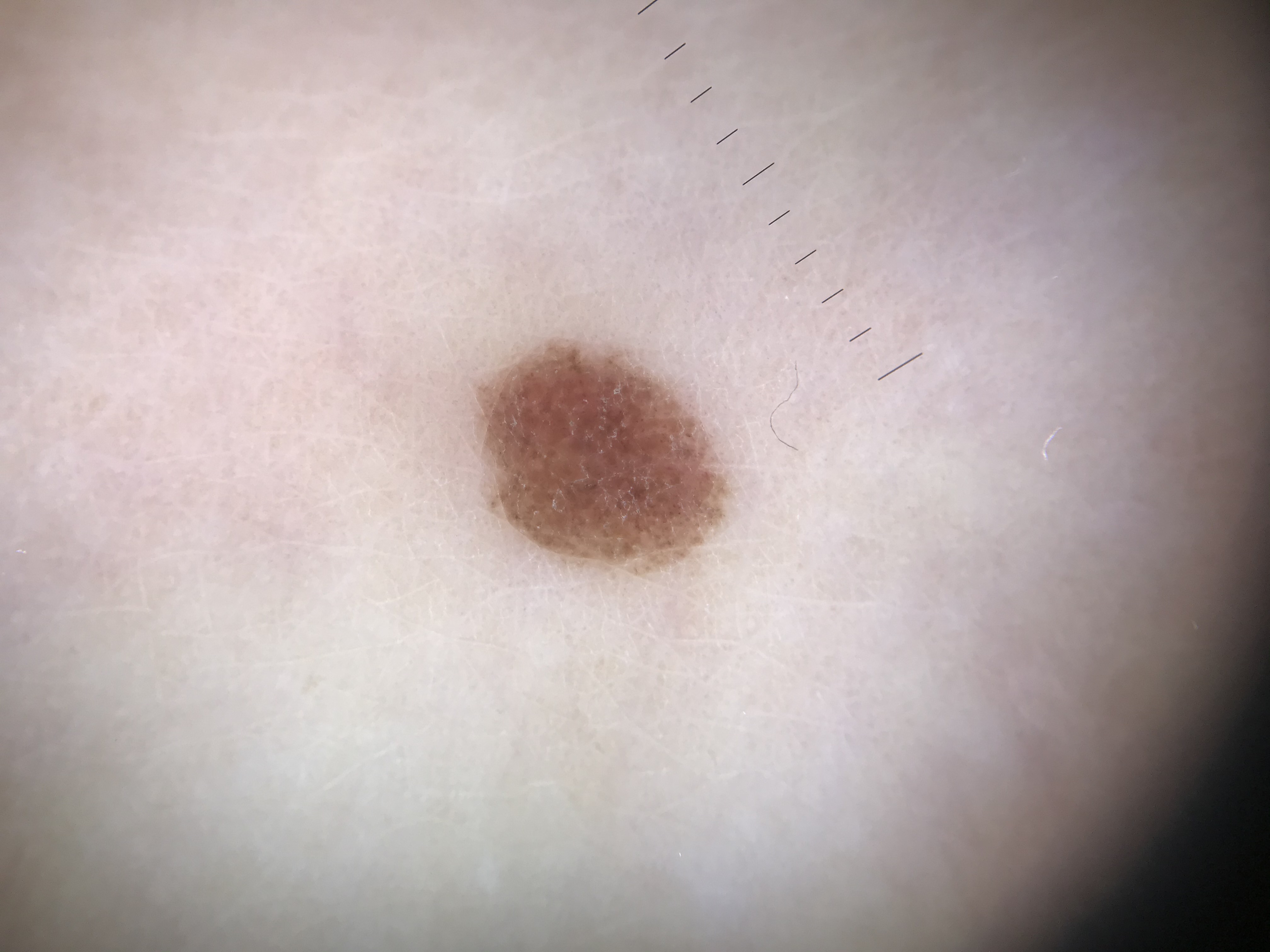{"diagnosis": {"name": "compound nevus", "code": "cb", "malignancy": "benign", "super_class": "melanocytic", "confirmation": "expert consensus"}}